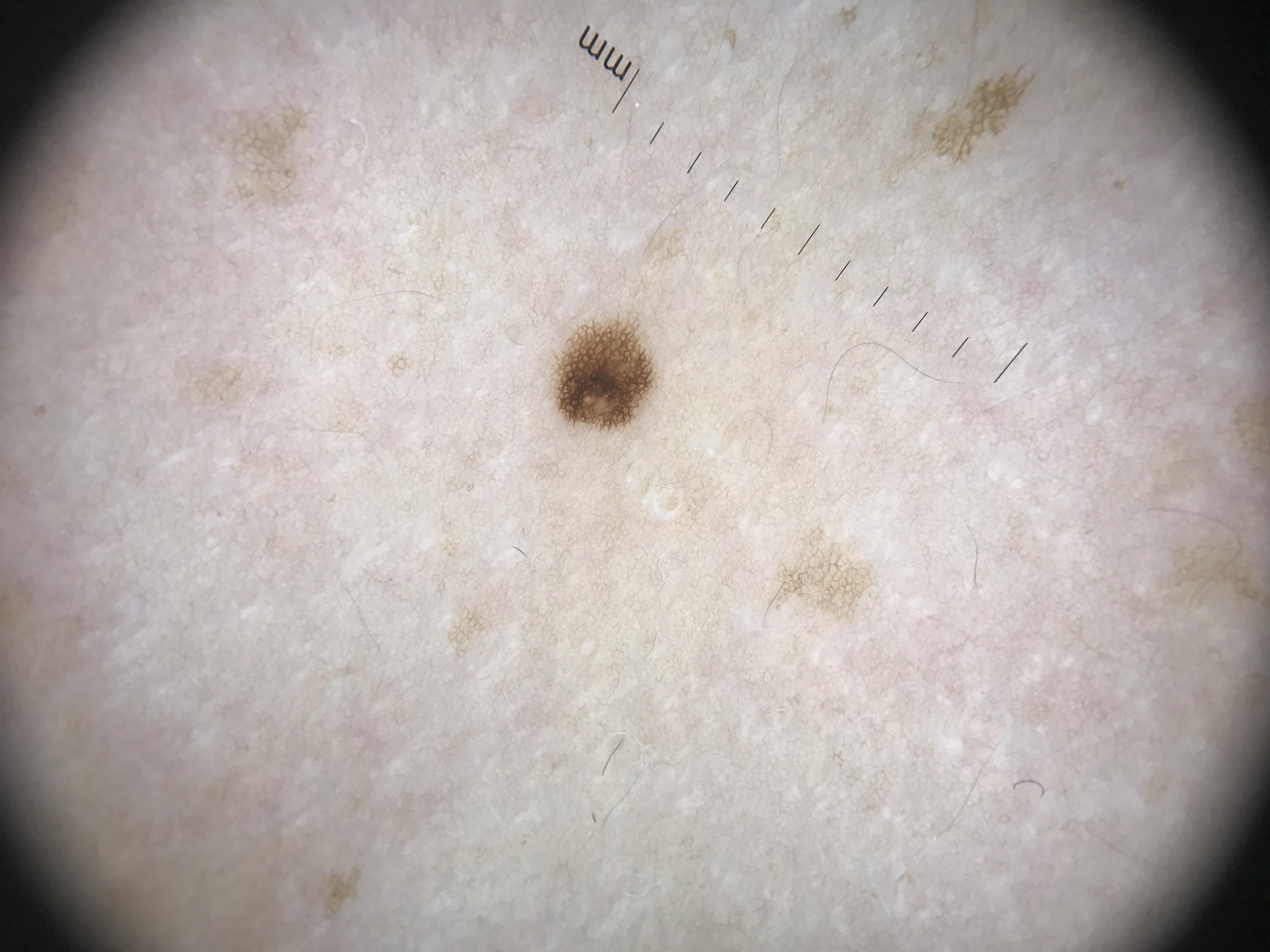Case:
The morphology is that of a banal lesion.
Conclusion:
Diagnosed as a junctional nevus.